No relevant lesion symptoms reported · texture is reported as raised or bumpy · the affected area is the head or neck · close-up view · reported duration is one to four weeks · the subject is a male aged 40–49.
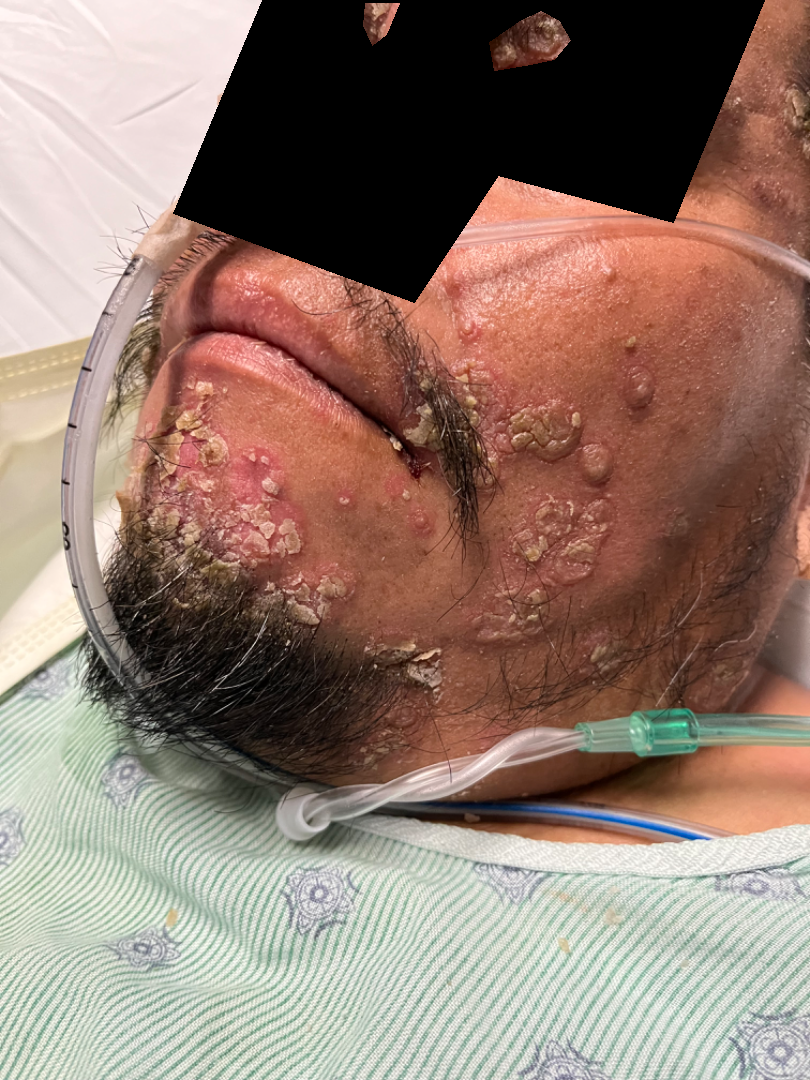Impression: The leading consideration is Seborrheic Dermatitis; an alternative is Pemphigus.